Close-up view; the contributor is 60–69, male; located on the front of the torso and back of the torso — 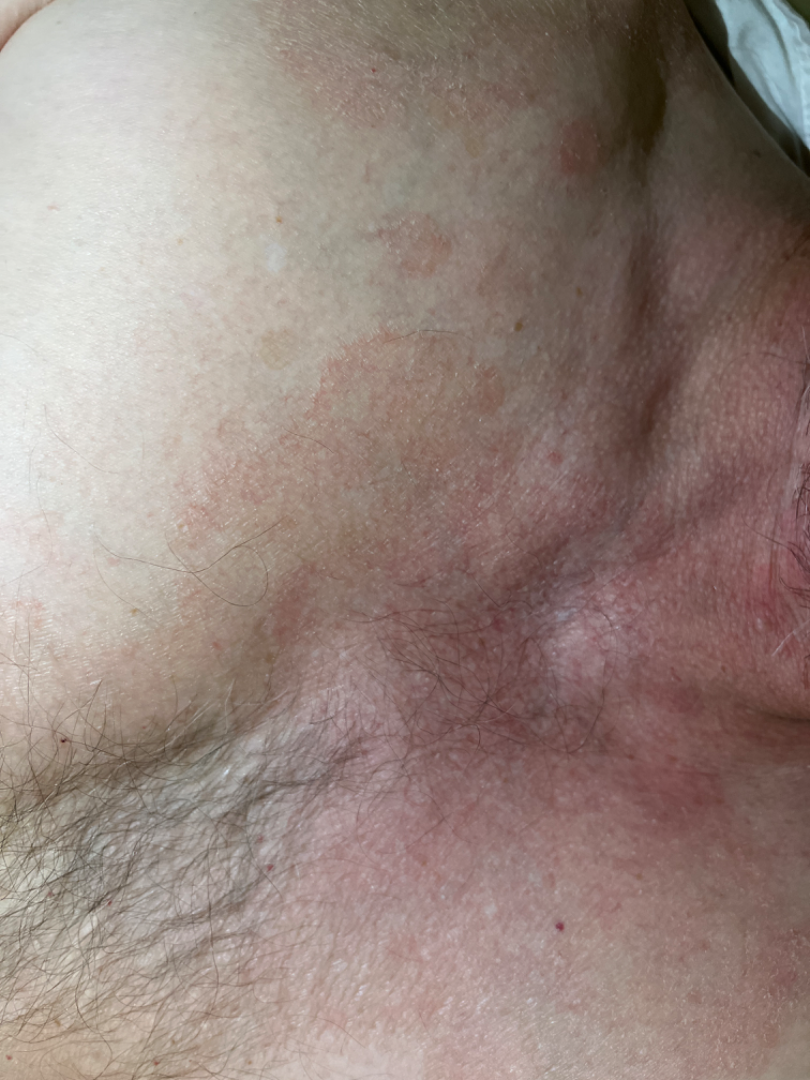  patient_category: a rash
  texture: flat
  differential:
    leading:
      - Tinea Versicolor
    considered:
      - Eczema
    unlikely:
      - Photodermatitis